A dermatoscopic image of a skin lesion.
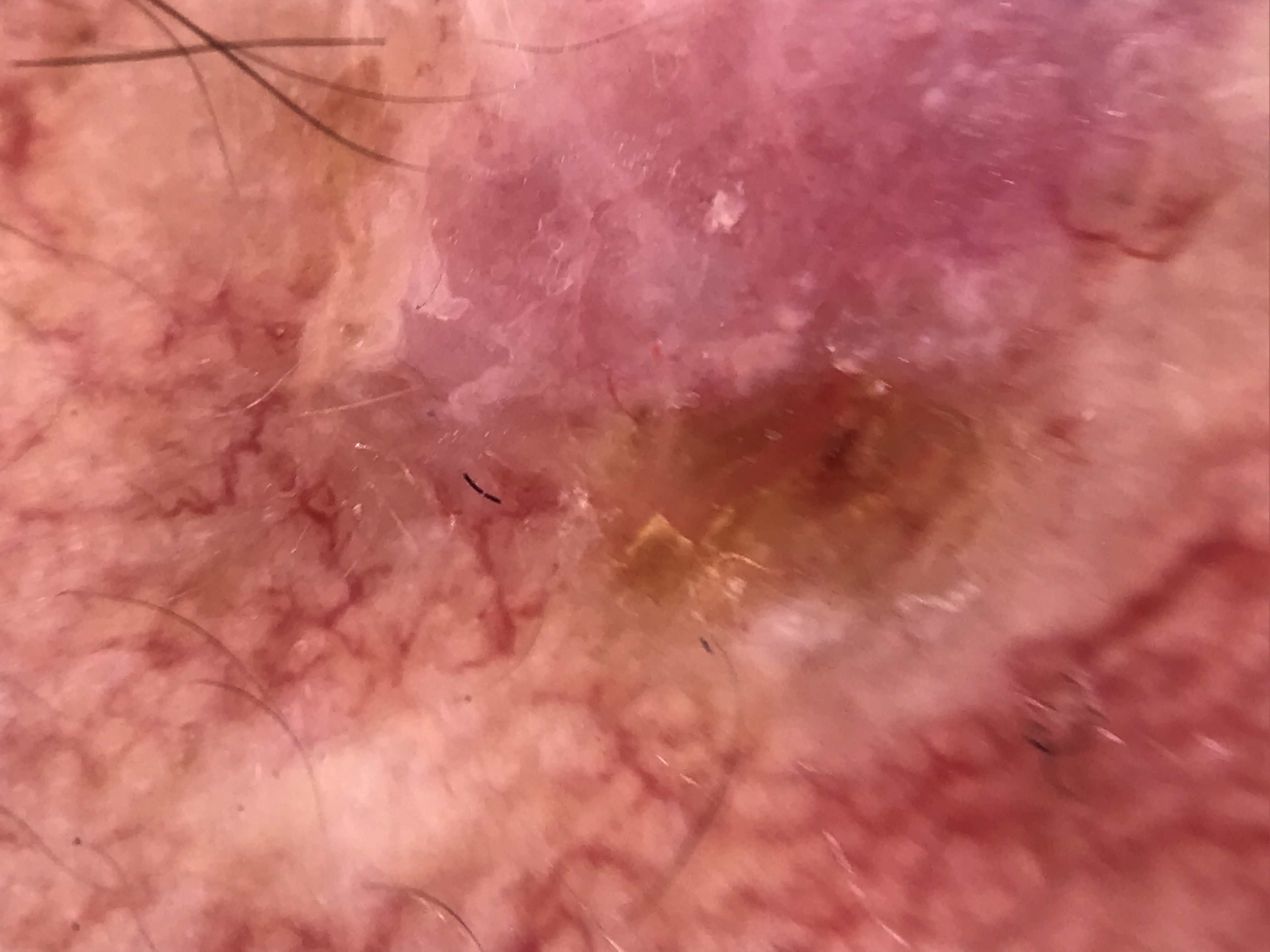diagnostic label: basal cell carcinoma (biopsy-proven)